Close-up view:
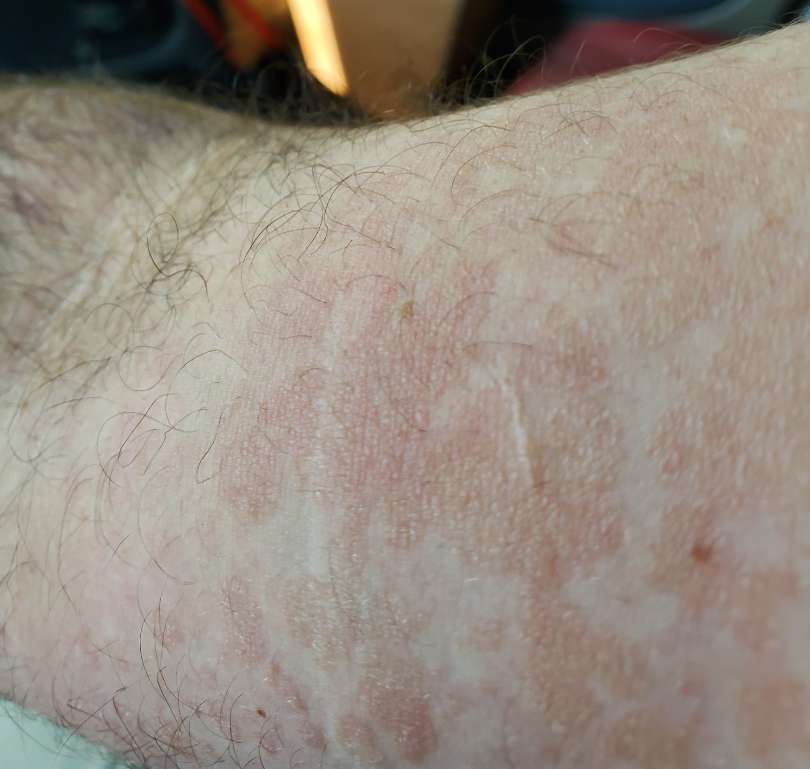| field | value |
|---|---|
| assessment | could not be assessed |